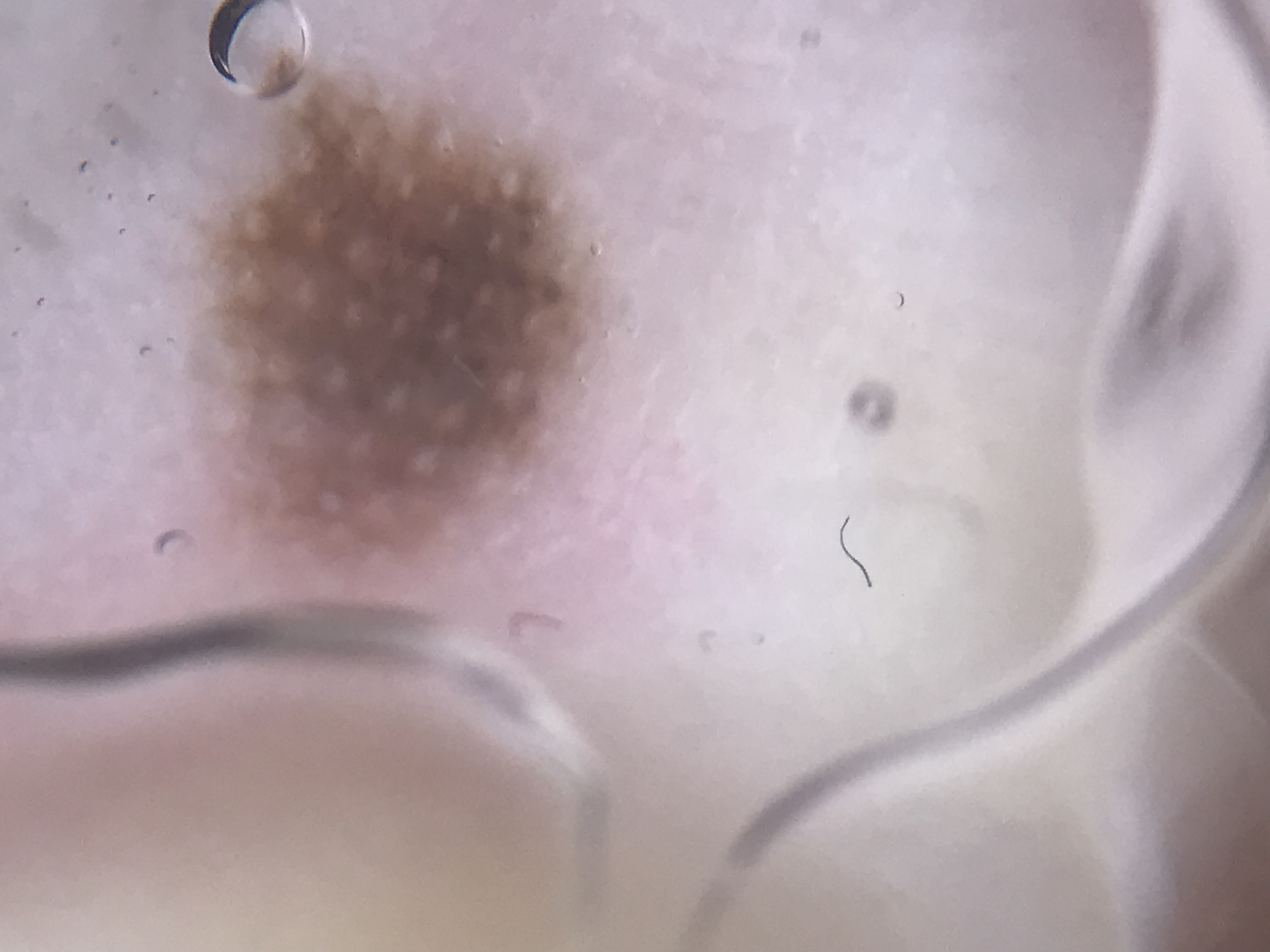class — acral junctional nevus (expert consensus)